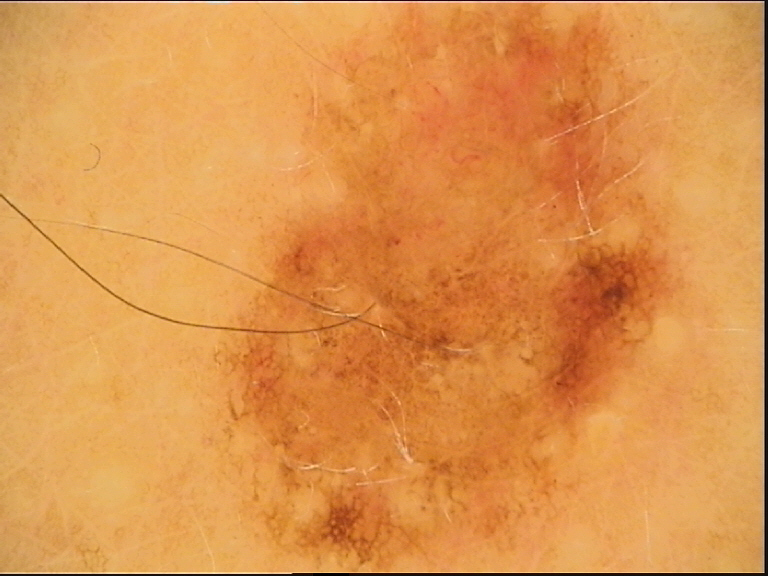A dermoscopy image of a single skin lesion. Consistent with a dysplastic compound nevus.